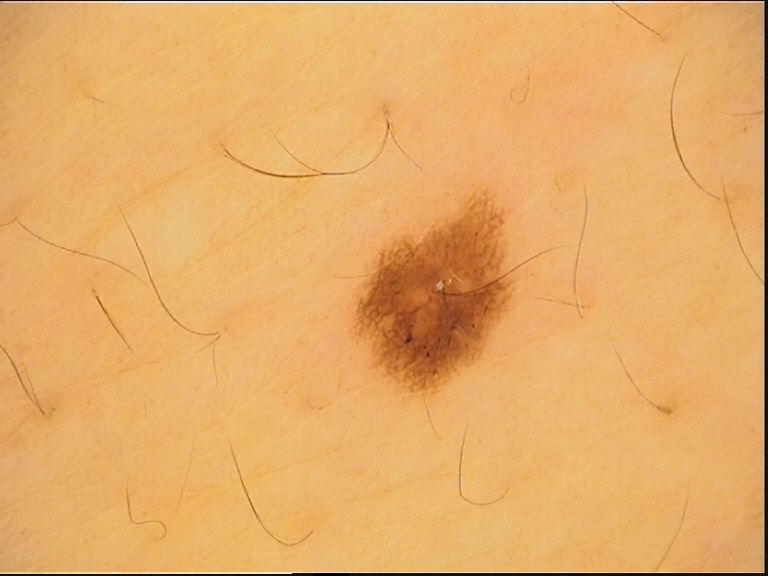image type = dermatoscopy; assessment = dysplastic junctional nevus (expert consensus).